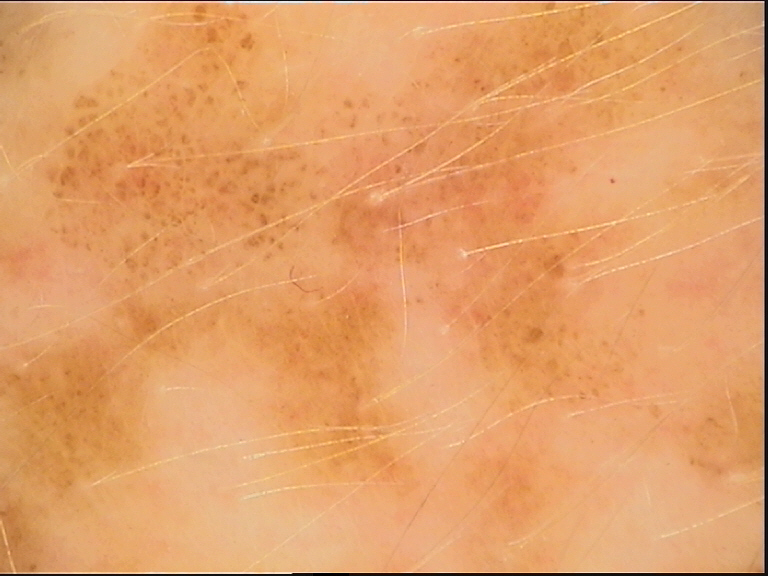| feature | finding |
|---|---|
| modality | dermoscopy |
| class | dysplastic junctional nevus (expert consensus) |